A dermoscopic view of a skin lesion:
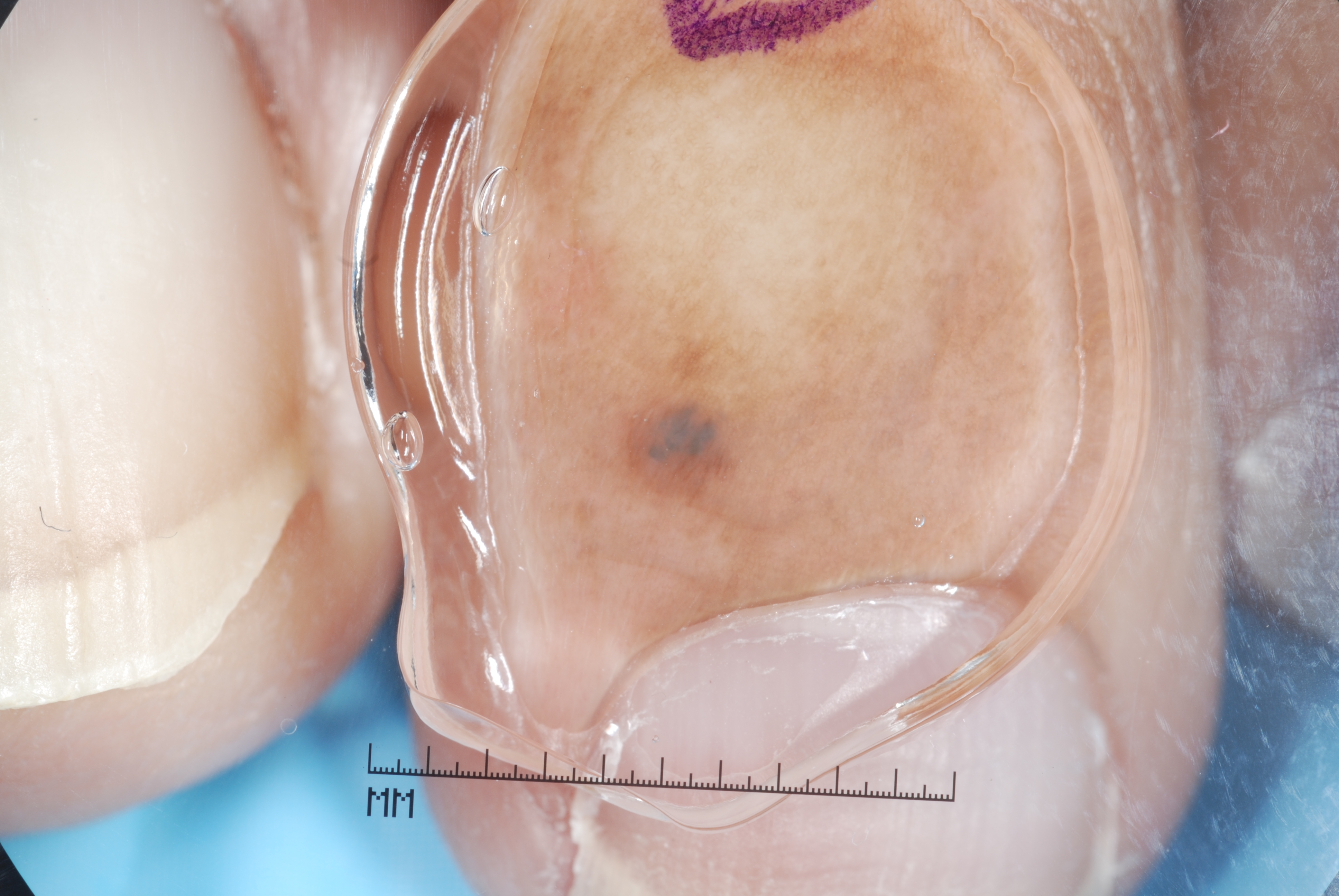Findings:
With coordinates (x1, y1, x2, y2), the lesion spans <box>621, 386, 748, 519</box>. Dermoscopic assessment notes no pigment network, milia-like cysts, streaks, or negative network.
Conclusion:
Diagnosed as a melanocytic nevus, a benign lesion.